The photograph is a close-up of the affected area, the affected area is the leg.
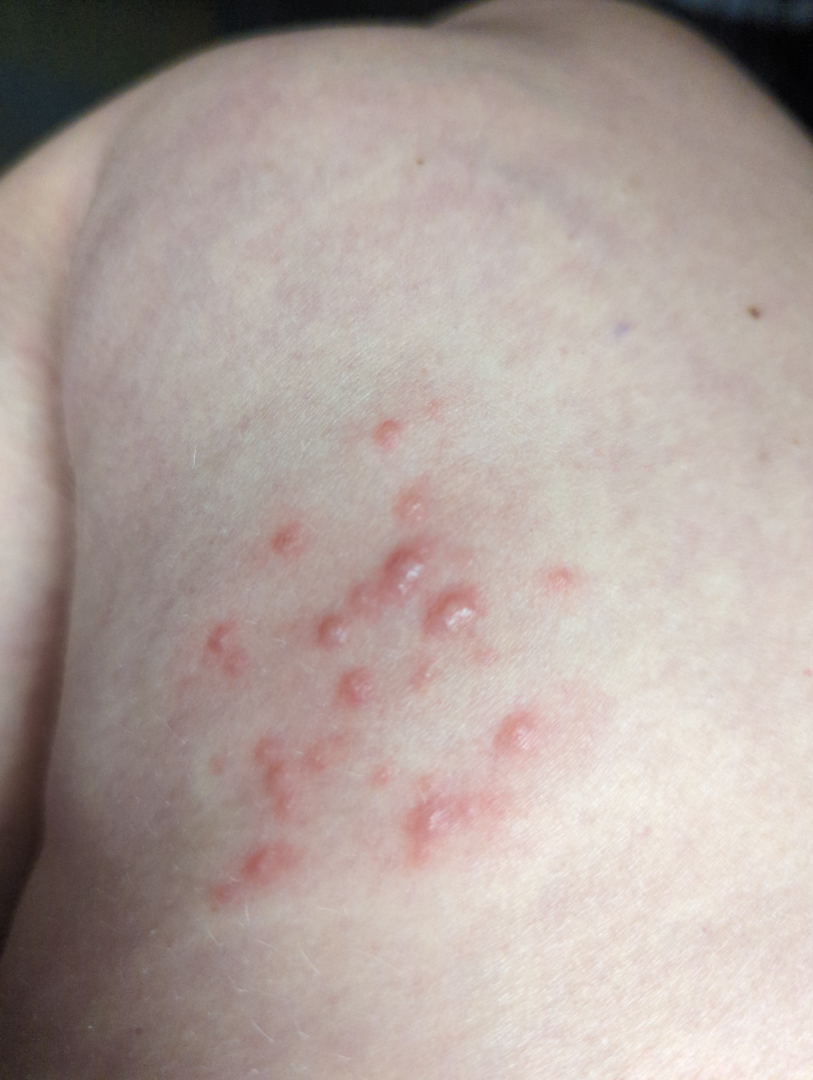Q: What is the differential diagnosis?
A: favoring Herpes Zoster